The photo was captured at an angle; located on the arm: 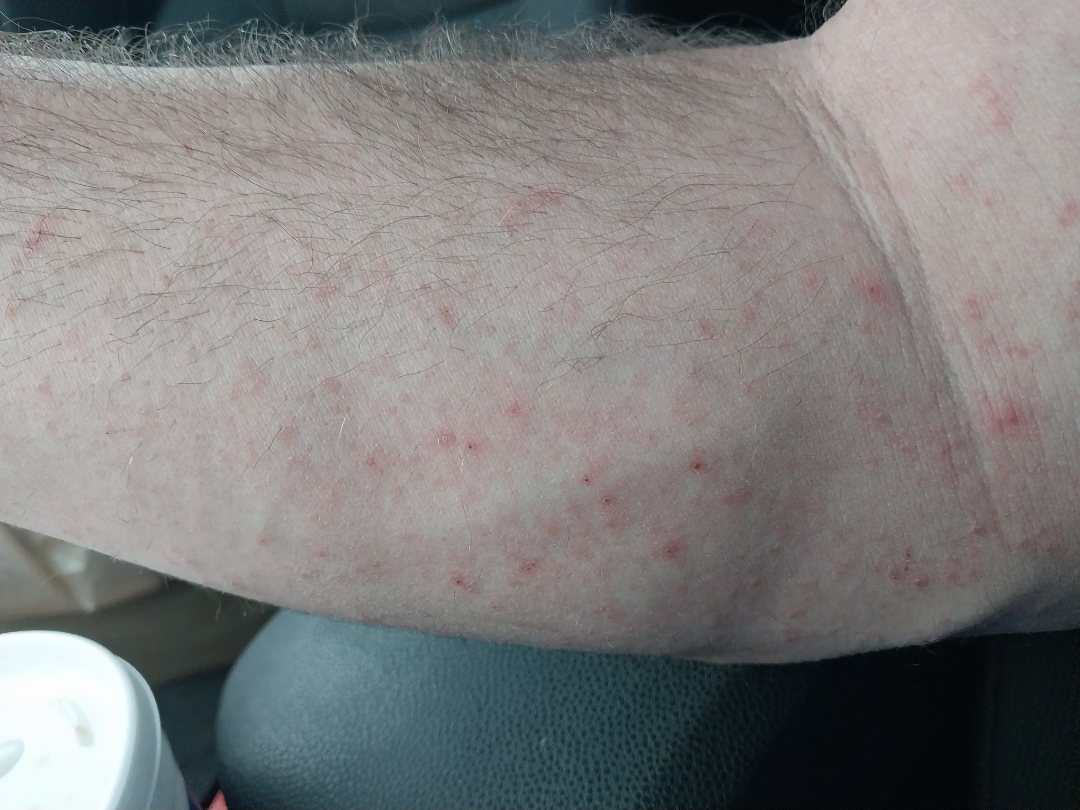assessment: could not be assessed.